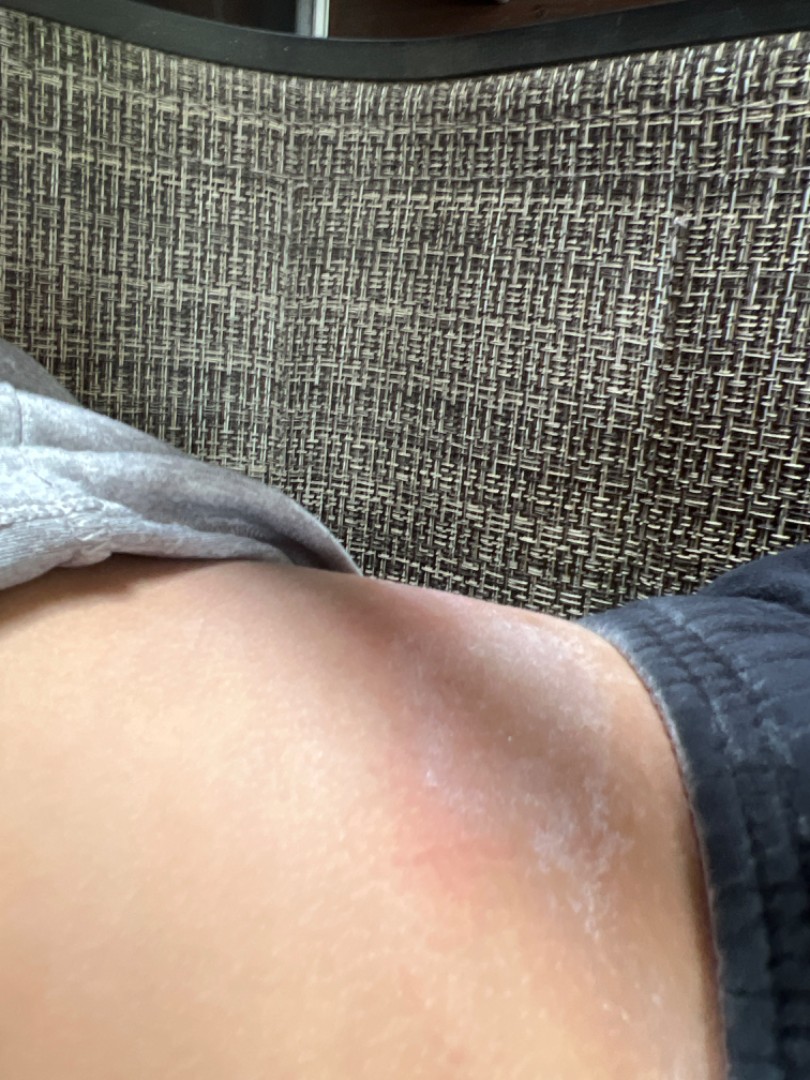skin tone: Fitzpatrick skin type IV
framing: at an angle
associated systemic symptoms: none reported
body site: front of the torso
lesion texture: raised or bumpy
history: about one day
assessment: the primary impression is Allergic Contact Dermatitis; the differential also includes Irritant Contact Dermatitis